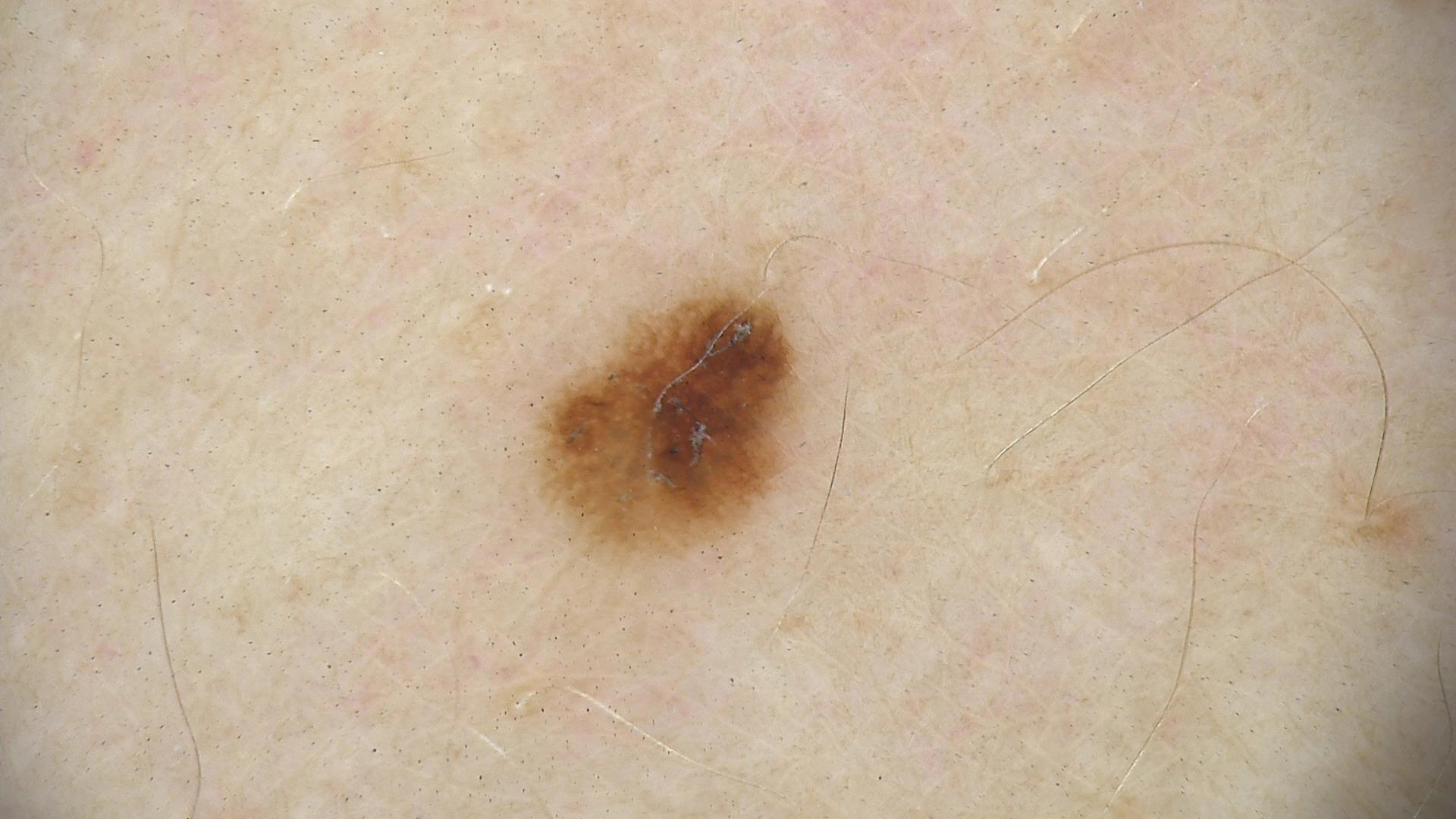The diagnosis was a benign lesion — a dysplastic junctional nevus.